Texture is reported as raised or bumpy. The lesion involves the leg. A close-up photograph. The patient considered this a rash. Present for one to four weeks.
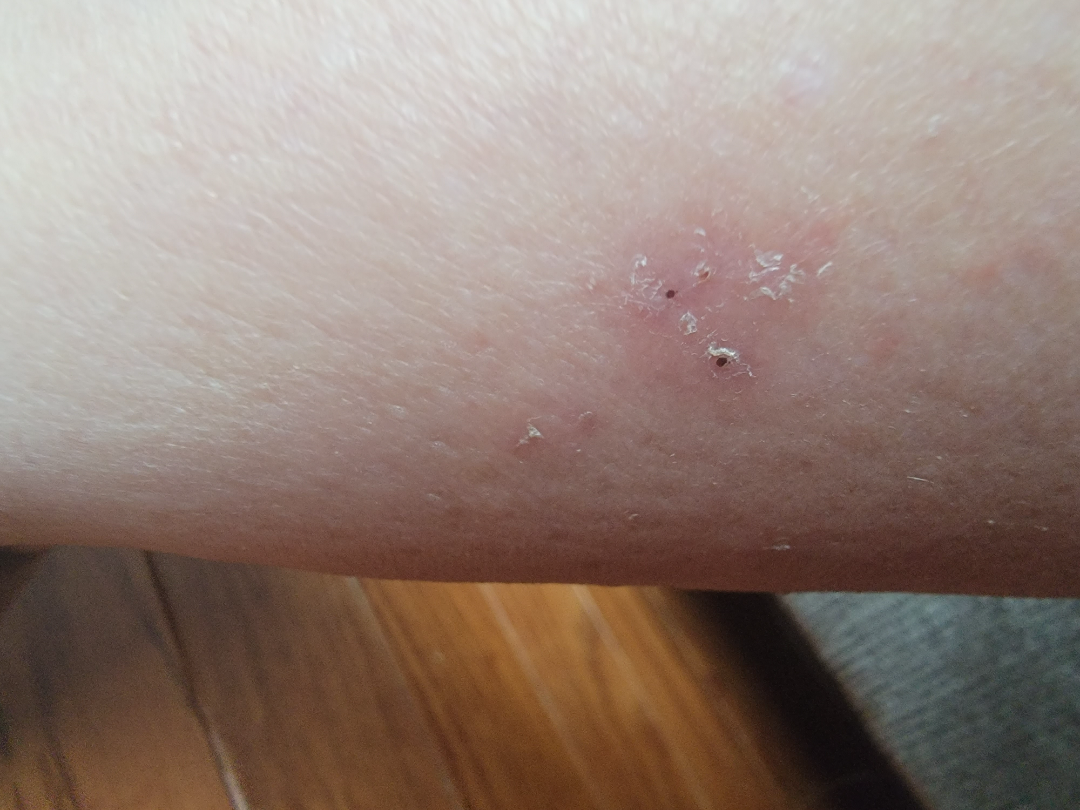Impression:
The differential, in no particular order, includes Acute and chronic dermatitis and Irritant Contact Dermatitis.